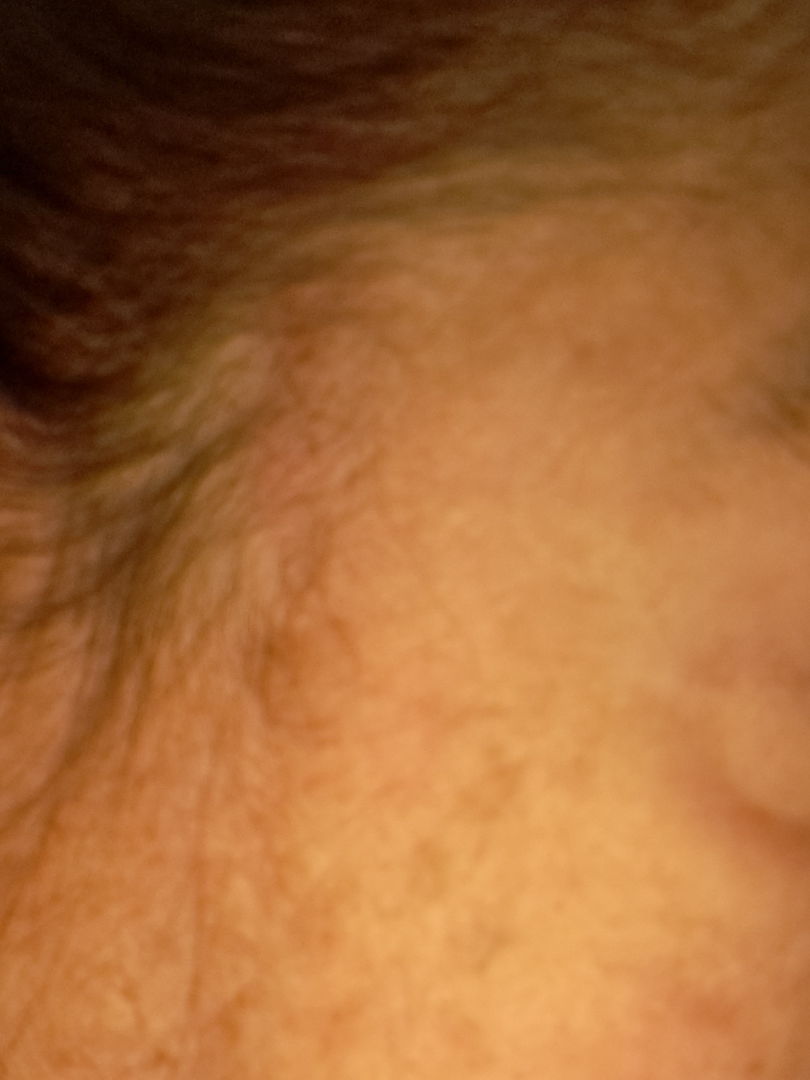Assessment: The reviewing dermatologist was unable to assign a differential diagnosis from the image. Clinical context: Located on the head or neck. Fitzpatrick phototype IV. This is a close-up image. The patient indicates associated fatigue. Texture is reported as raised or bumpy. Present for more than one year. The patient is female. The patient indicates enlargement, itching and bothersome appearance.